Dermoscopy of a skin lesion.
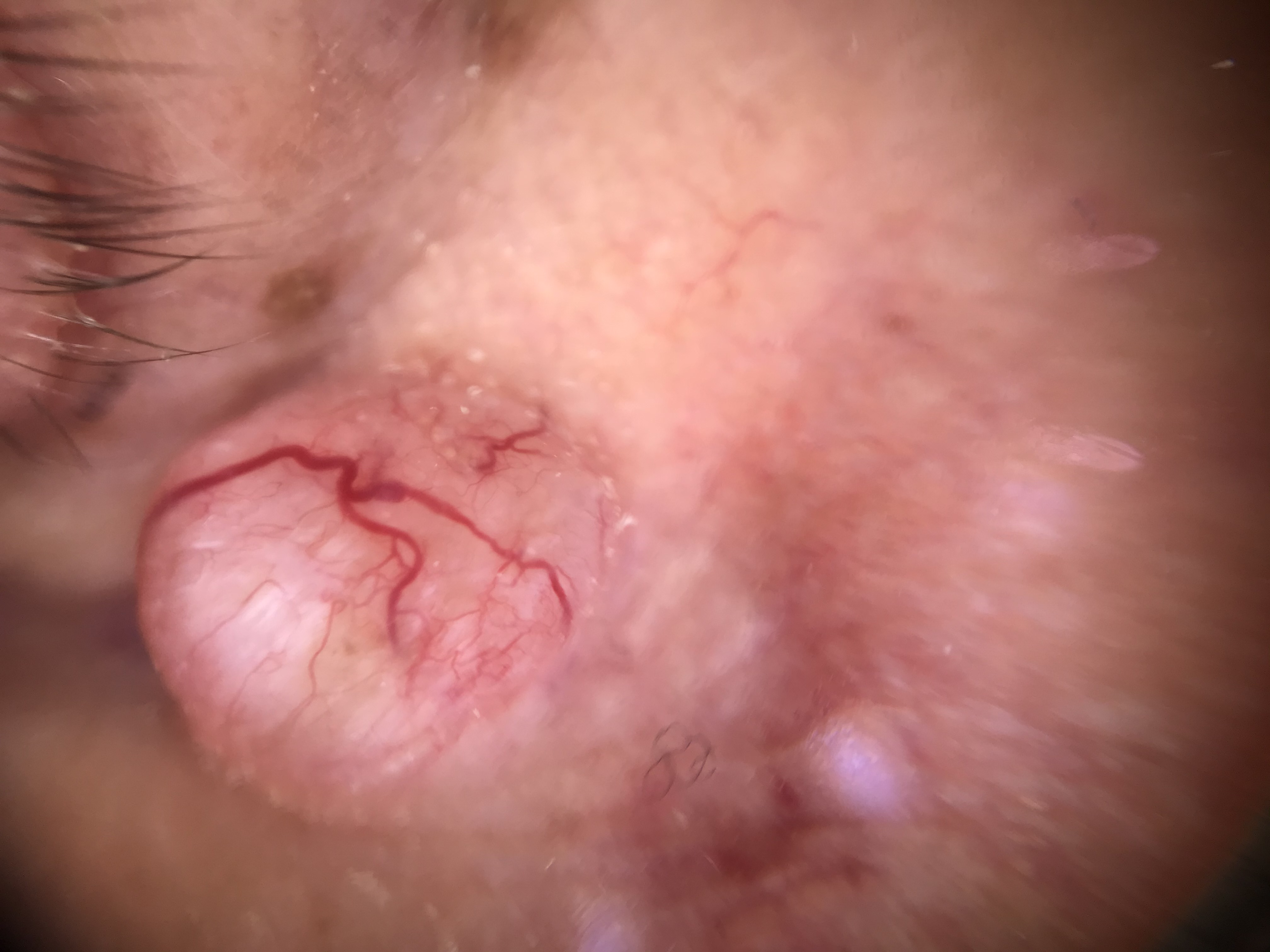Findings:
- classification — keratinocytic
- label — basal cell carcinoma (biopsy-proven)